The affected area is the leg; female contributor, age 30–39; the photograph was taken at a distance.
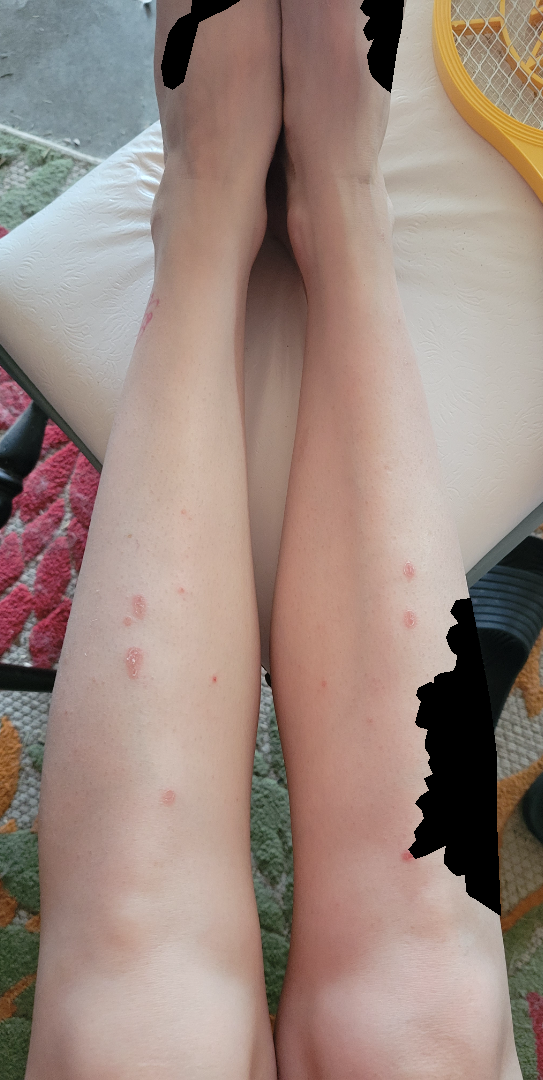Findings: On dermatologist assessment of the image: the leading consideration is Psoriasis; lower on the differential is Eczema; less probable is Drug Rash; less likely is Pityriasis lichenoides; a remote consideration is Lichen planus/lichenoid eruption.